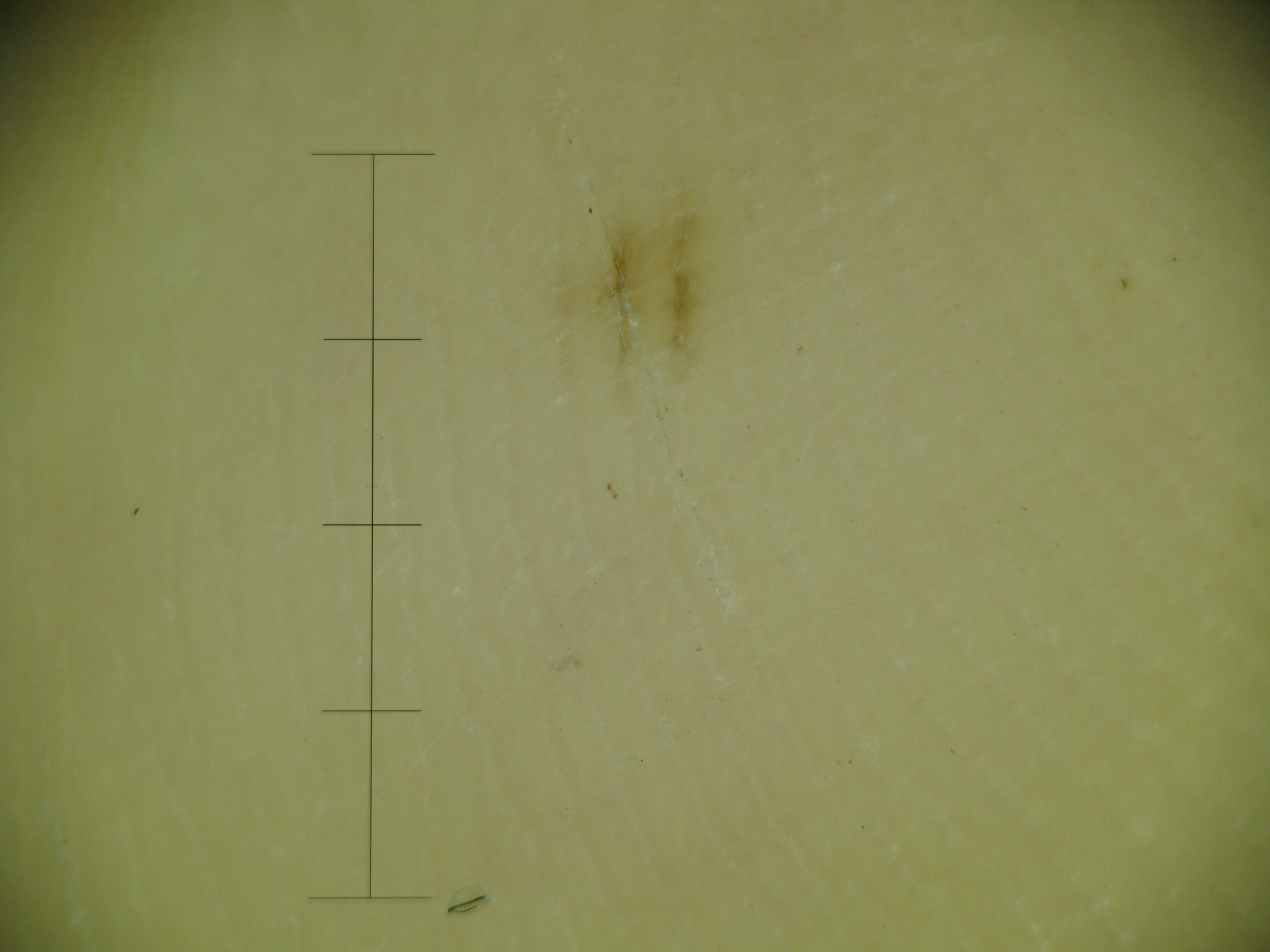A dermoscopic image of a skin lesion.
The morphology is that of a banal lesion.
Classified as an acral junctional nevus.